Dermoscopy of a skin lesion. The patient is a male approximately 50 years of age — 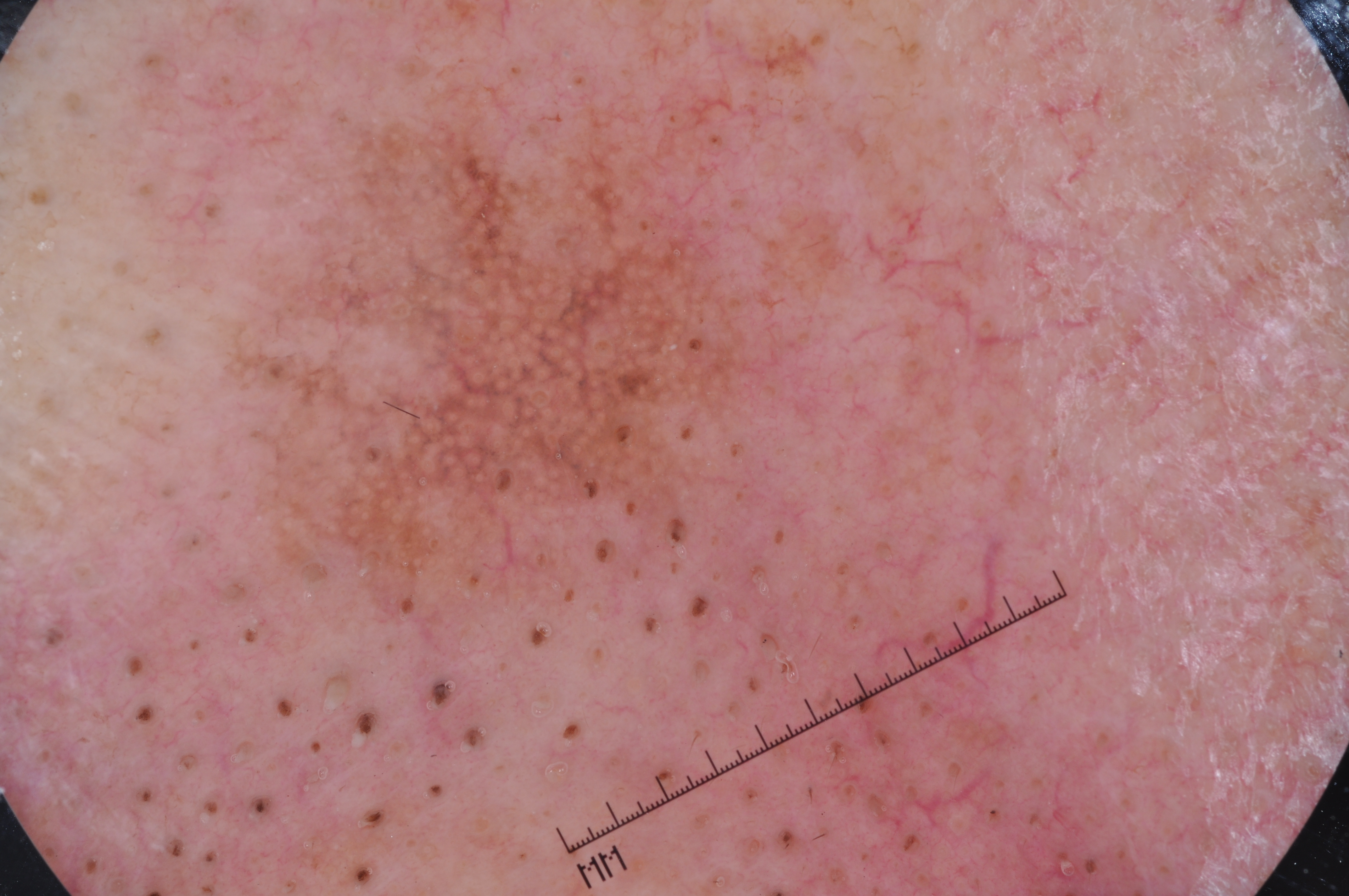extent = ~20% of the field
bounding box = [214,69,751,634]
dermoscopic findings = milia-like cysts; absent: pigment network, negative network, and streaks
diagnosis = a melanoma